The patient is Fitzpatrick phototype II · a male subject about 75 years old: 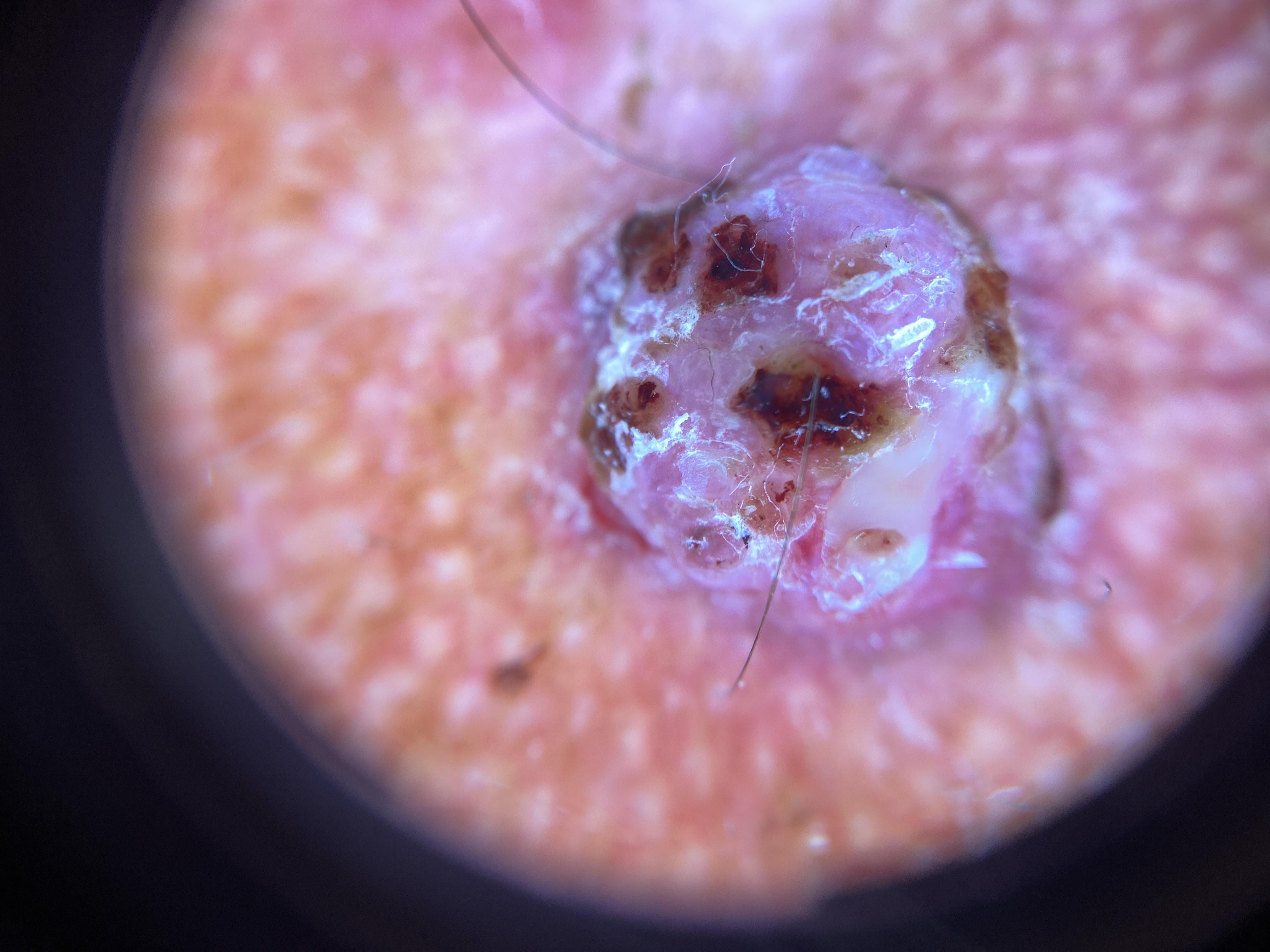The lesion was found on the head or neck. The biopsy diagnosis was a basal cell carcinoma.